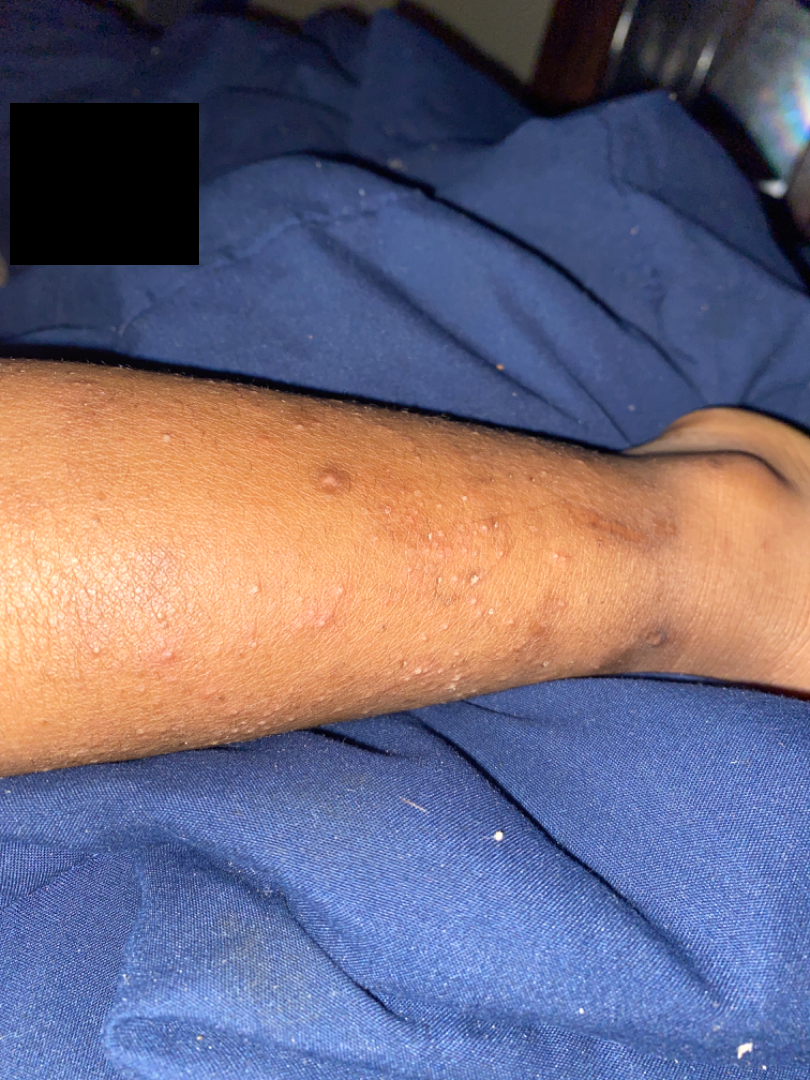| key | value |
|---|---|
| differential | in keeping with Chronic dermatitis, NOS |